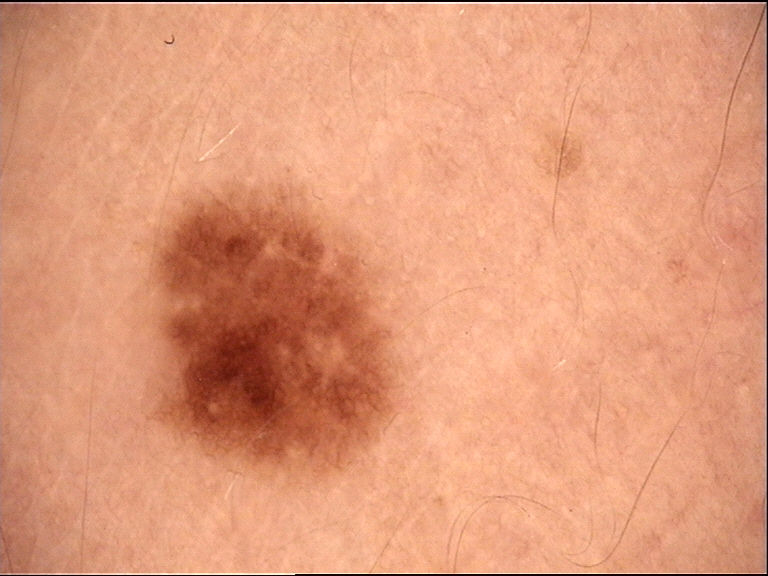Impression: Diagnosed as a dysplastic junctional nevus.